The patient is a female aged 18–29. The lesion involves the front of the torso and leg. This image was taken at an angle — 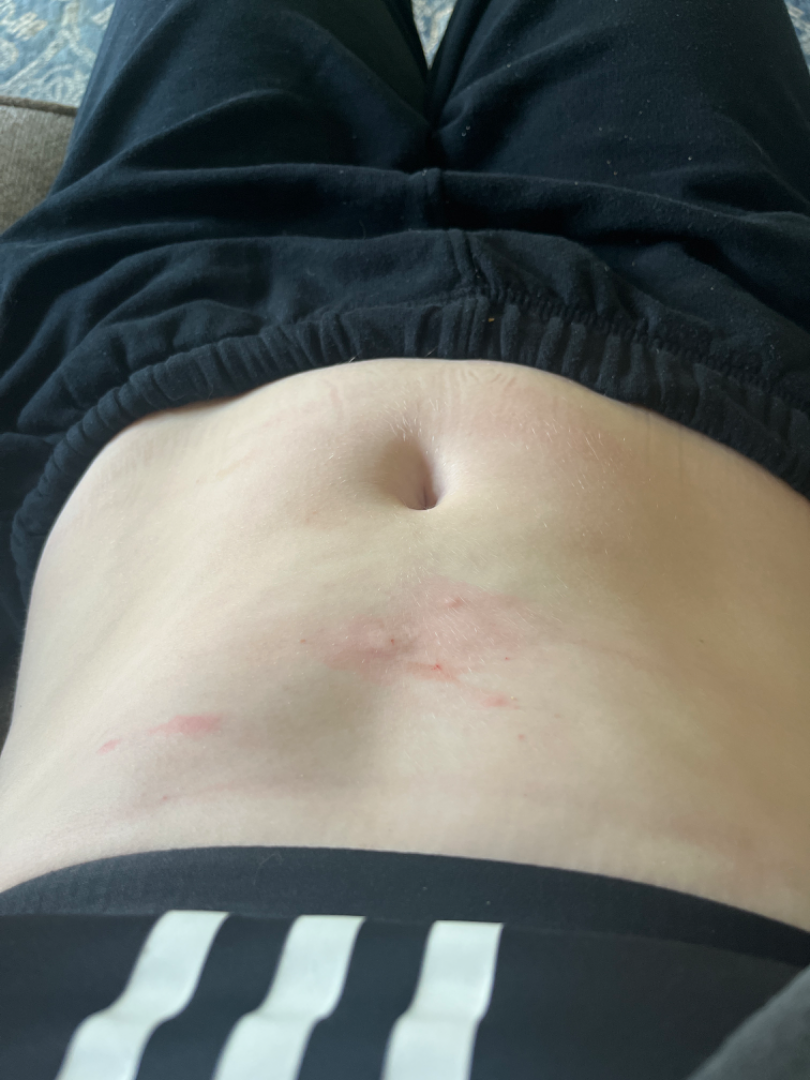On photographic review, Allergic Contact Dermatitis (leading).